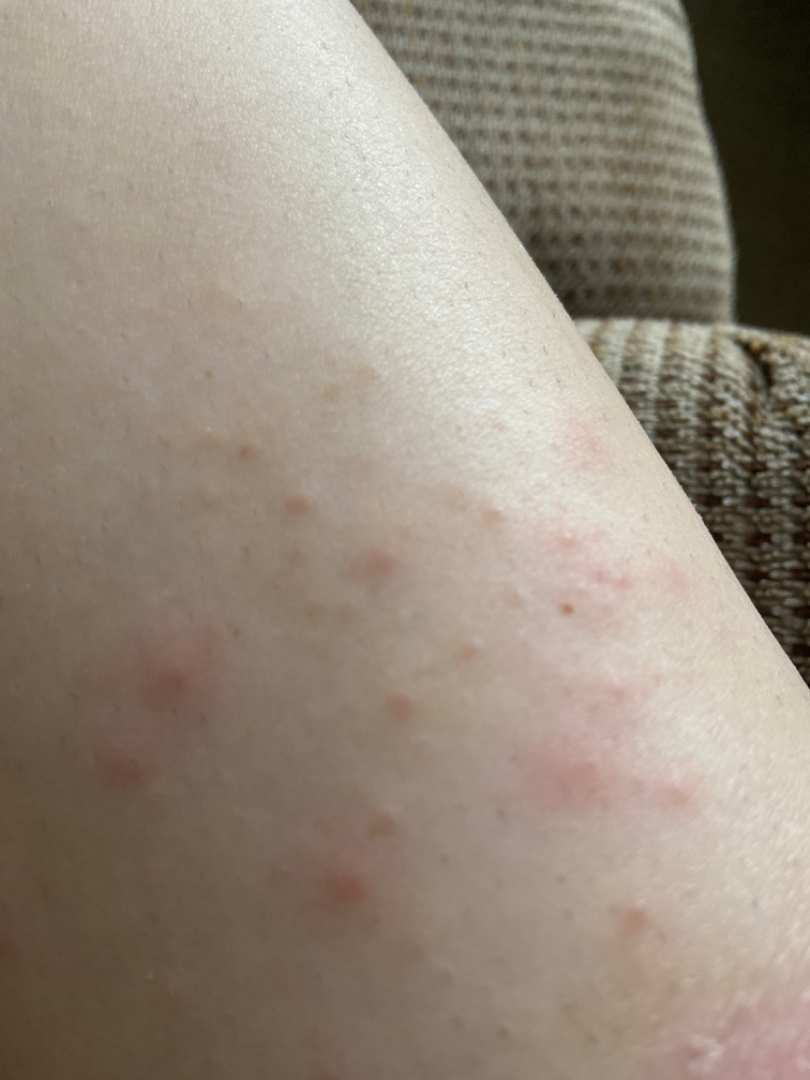* diagnostic considerations — reviewed remotely by one dermatologist: in keeping with Folliculitis